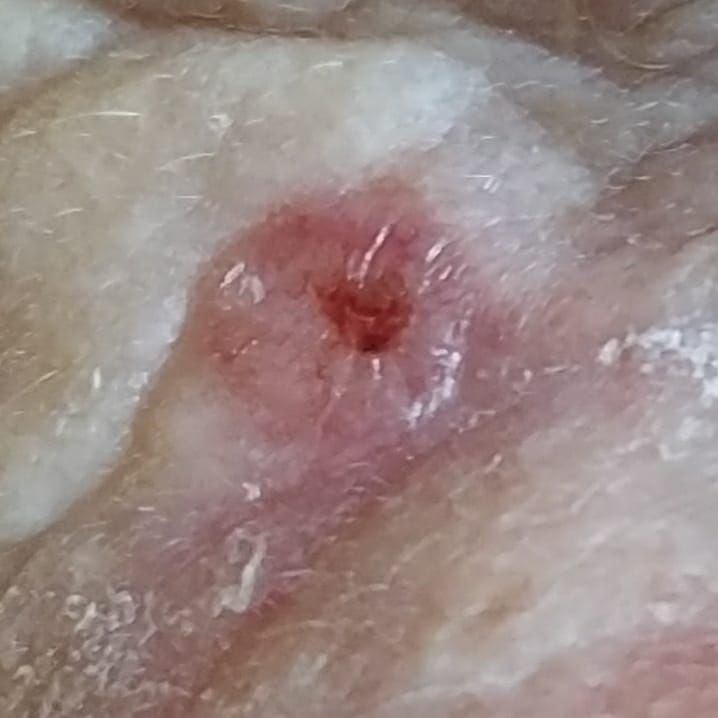skin type: I | image: smartphone clinical photo | body site: the face | lesion size: 6x5 mm | patient-reported symptoms: elevation, bleeding, pain, growth, itching / no change in appearance | pathology: basal cell carcinoma (biopsy-proven).